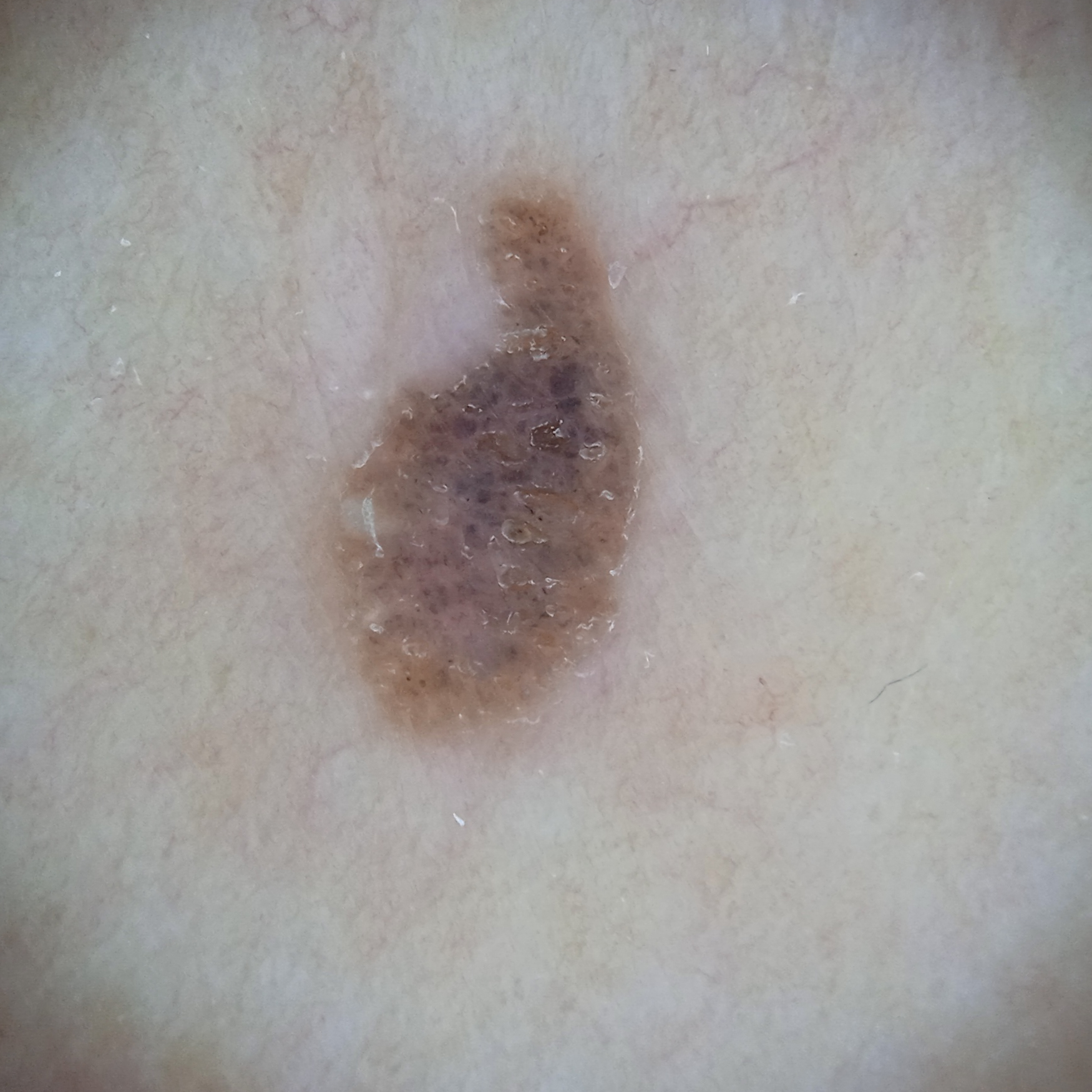sun reaction: skin tans without first burning | nevus count: few melanocytic nevi overall | subject: female, 60 years old | relevant history: a personal history of skin cancer, a personal history of cancer, no immunosuppression | image: dermoscopy | clinical context: research study (no referral diagnosis) | site: the torso | lesion size: 6.2 mm | assessment: seborrheic keratosis (dermatologist consensus).